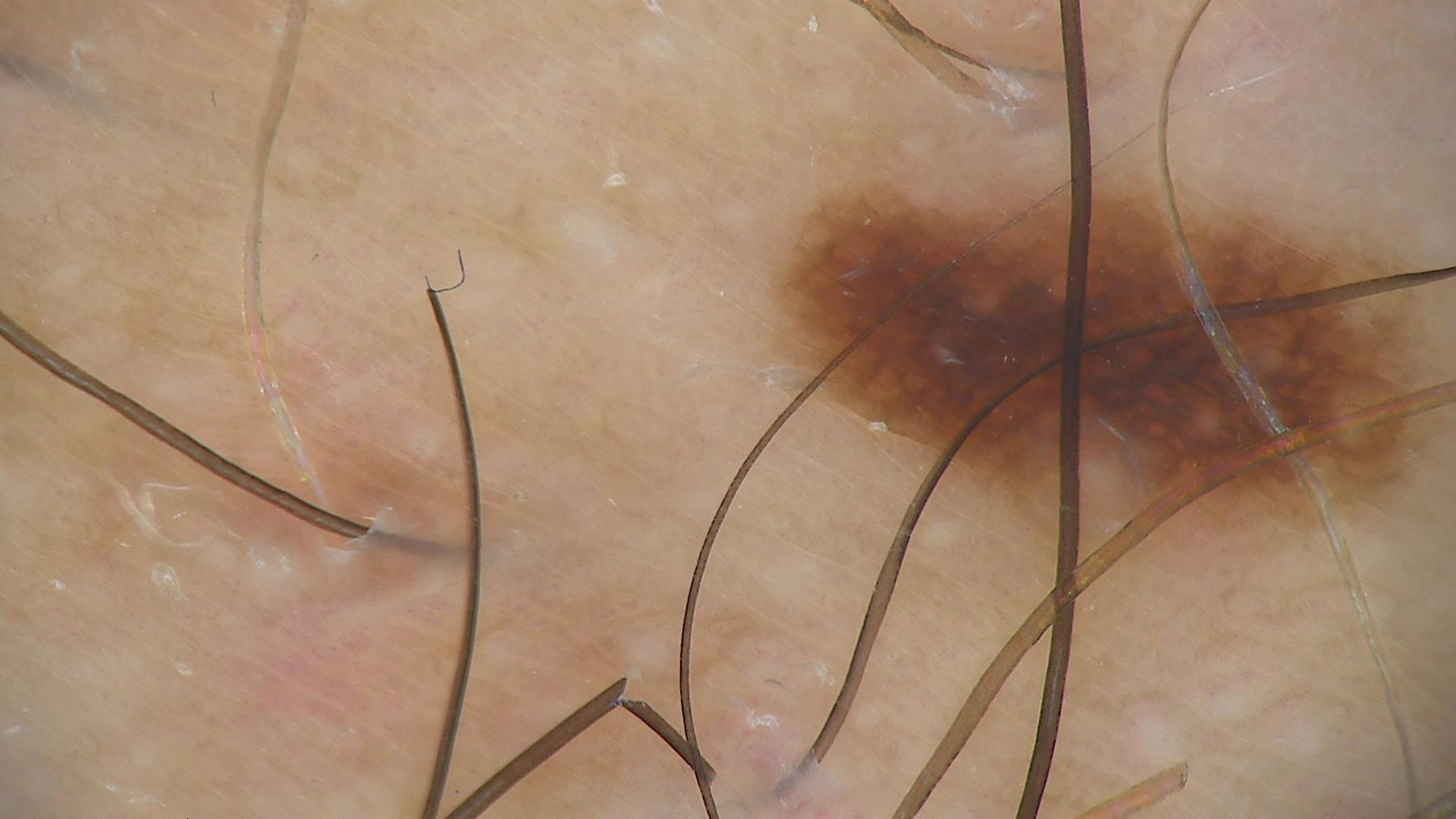Consistent with a dysplastic junctional nevus.